The condition has been present for one to four weeks · the lesion involves the leg · the contributor is 60–69, female · this is a close-up image · texture is reported as raised or bumpy · symptoms reported: itching — 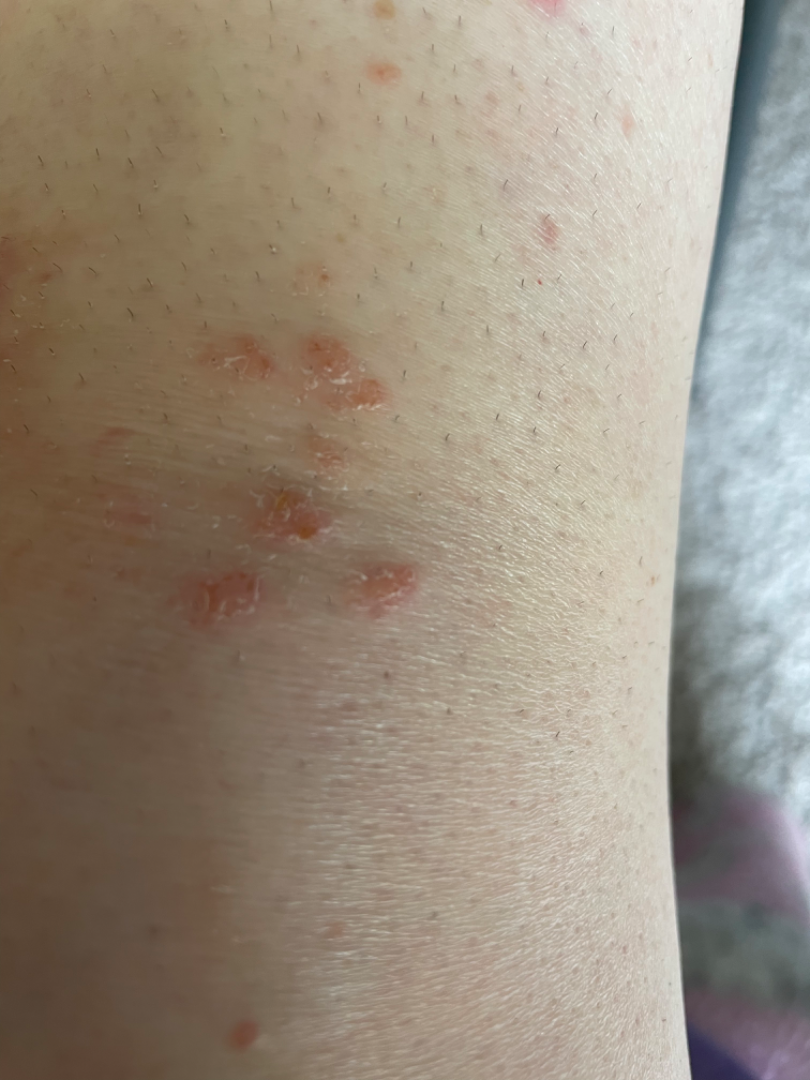differential = a single dermatologist reviewed the case: the primary impression is Impetigo; with consideration of Eczema.